Close-up view:
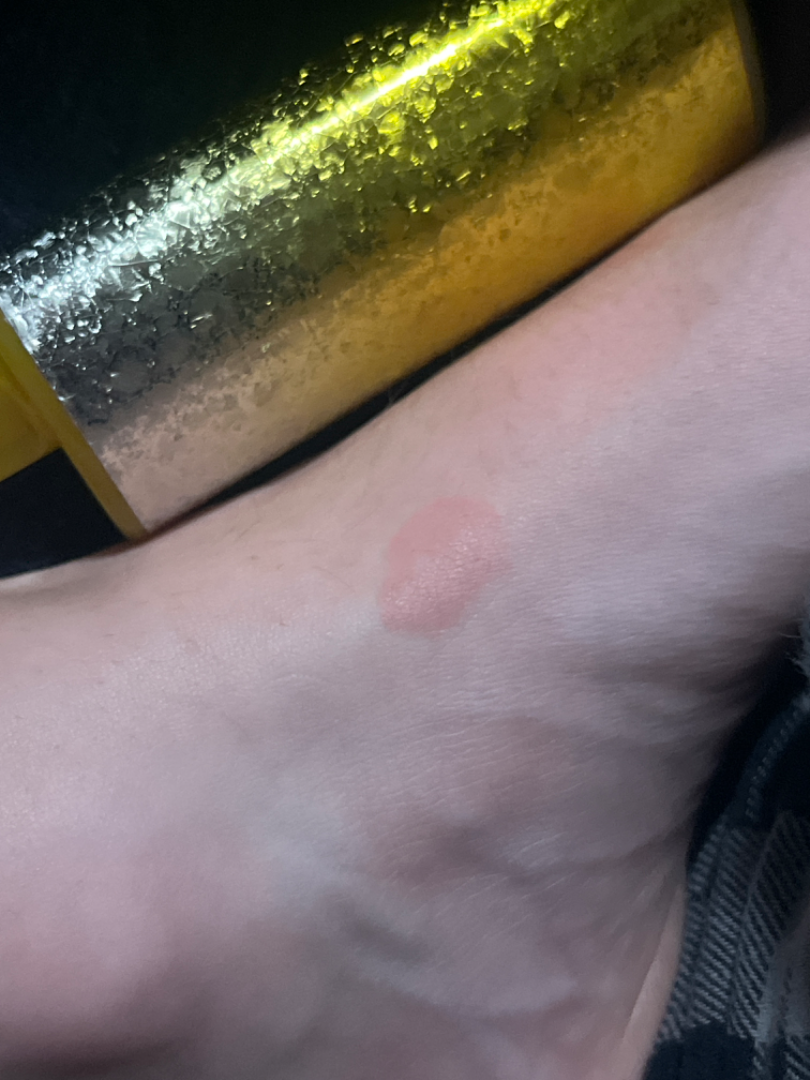Assessment:
The impression was split between Tinea, Eczema and Allergic Contact Dermatitis.